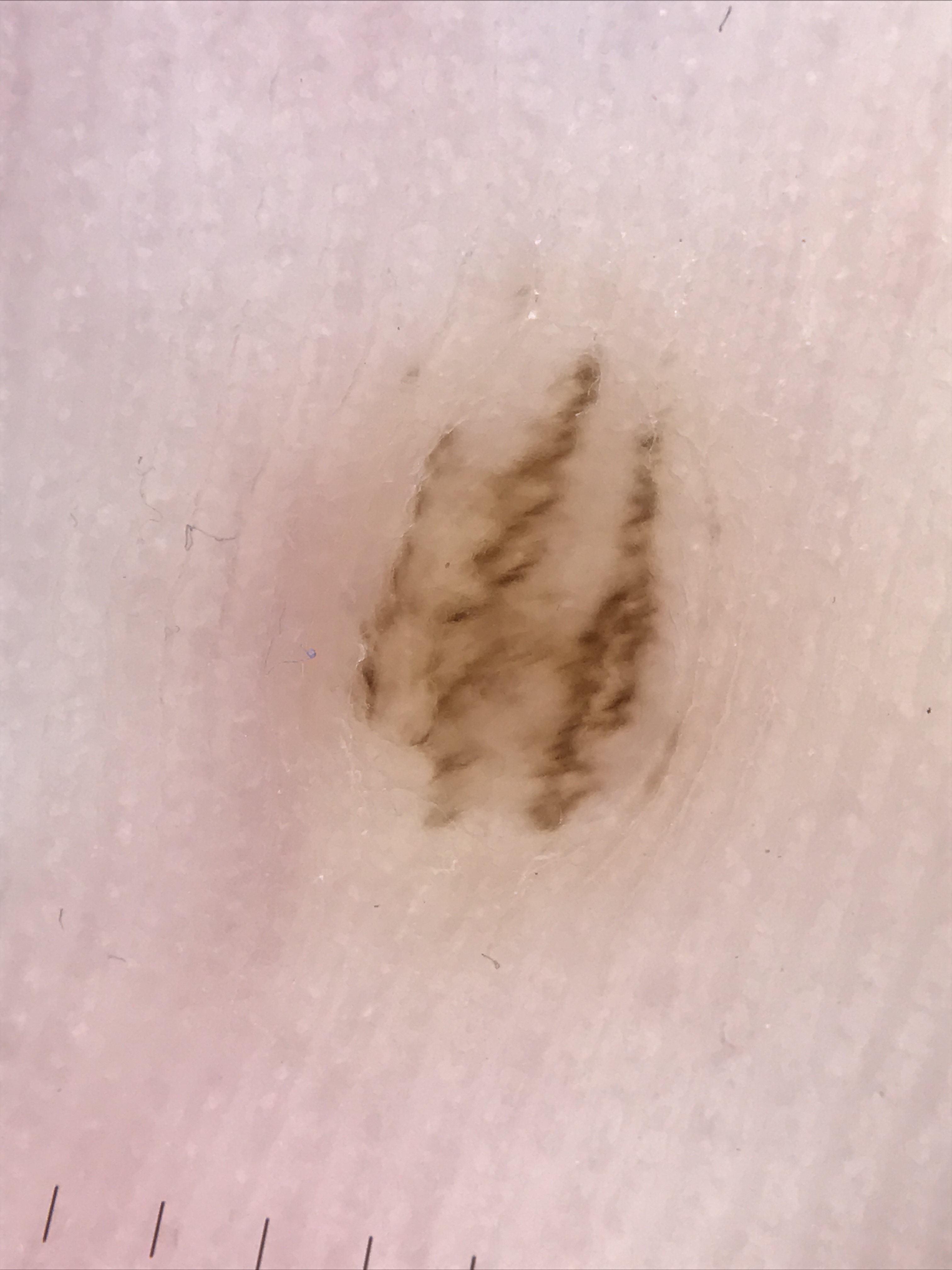class=acral compound nevus (expert consensus)